A skin lesion imaged with a dermatoscope.
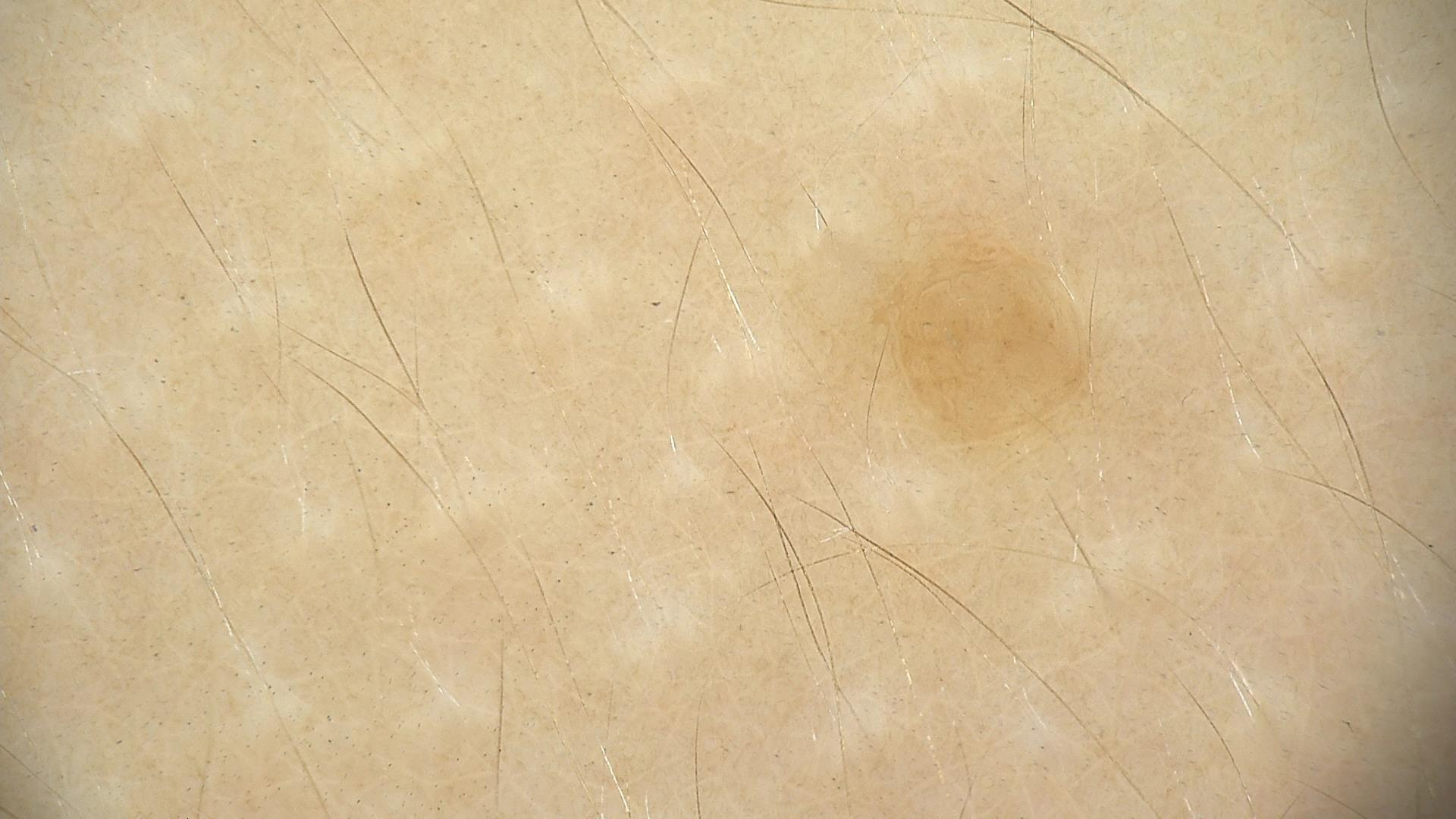Summary: The morphology is that of a banal lesion. Impression: Classified as a dermal nevus.